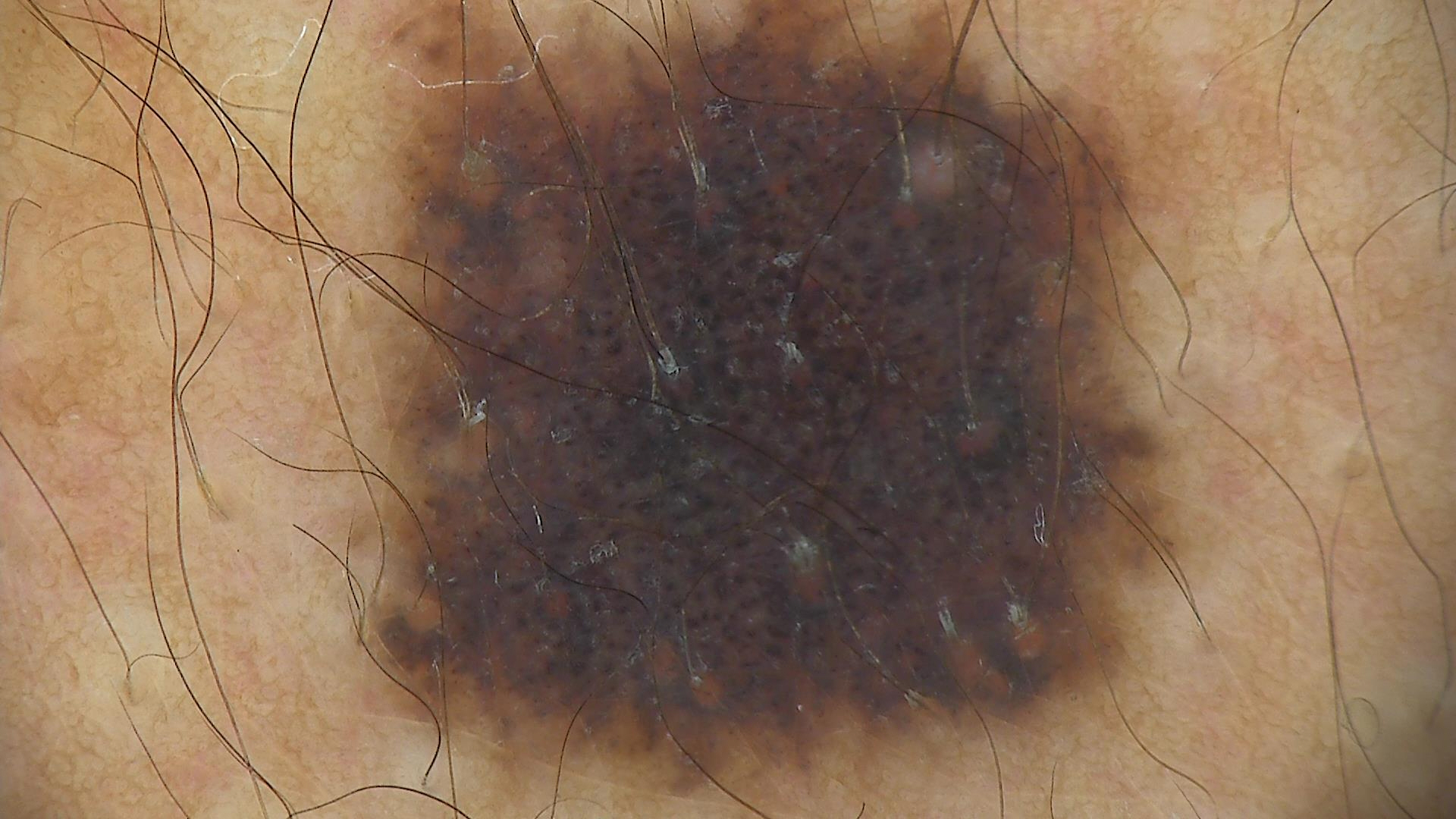The diagnosis was a congenital dysplastic compound nevus.